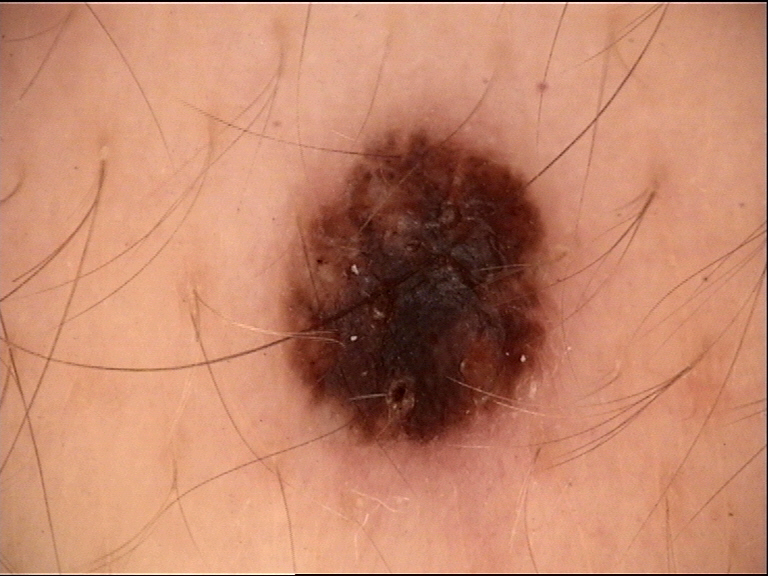A dermoscopic close-up of a skin lesion. The diagnosis was a dysplastic compound nevus.